The patient considered this a rash; the leg is involved; symptoms reported: bothersome appearance; the contributor is a male aged 40–49; the condition has been present for less than one week; a close-up photograph:
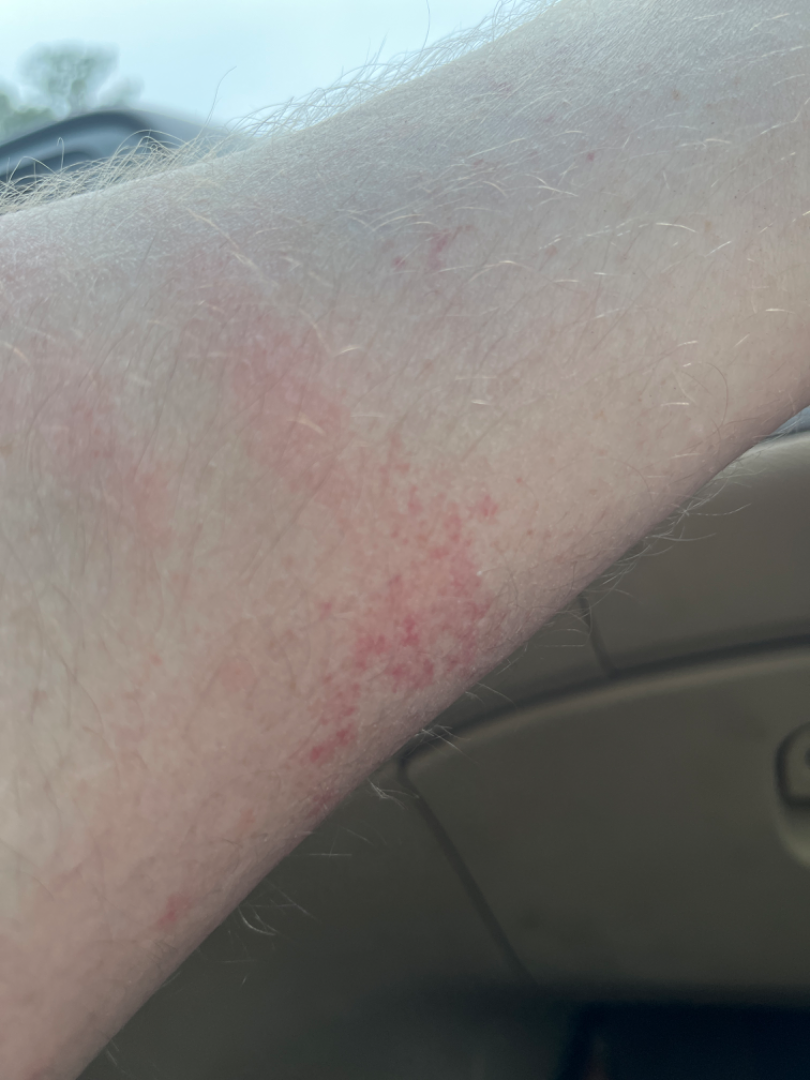On remote dermatologist review: Traumatic petechiae, Allergic Contact Dermatitis and Leukocytoclastic Vasculitis were considered with similar weight.